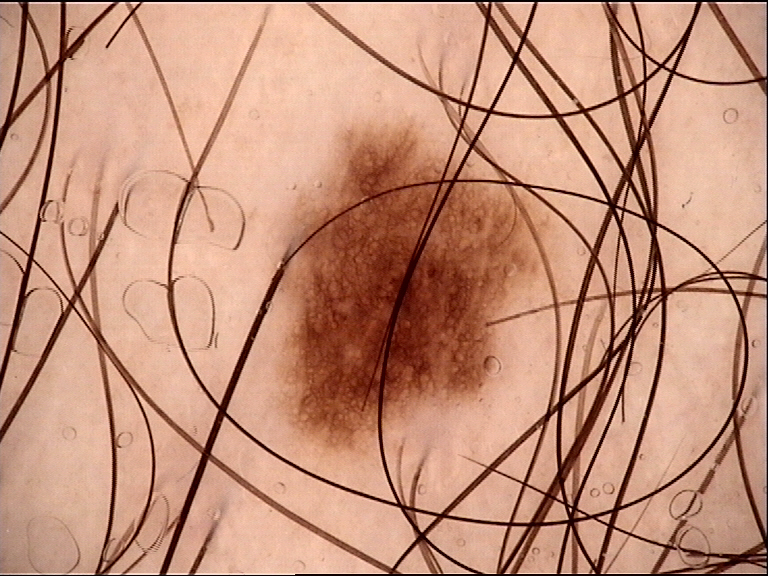Impression:
Diagnosed as a dysplastic junctional nevus.